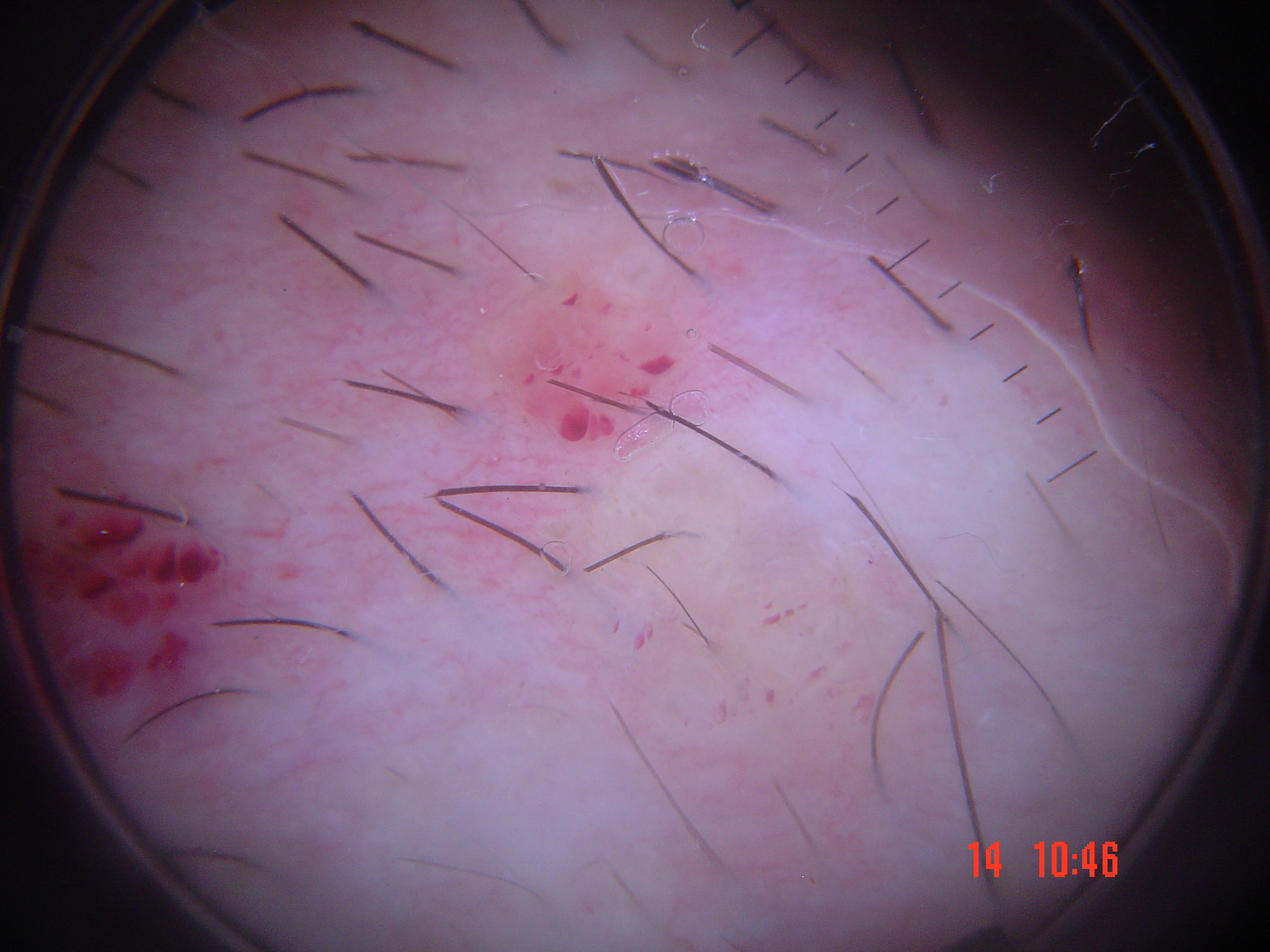Classified as a lymphangioma.